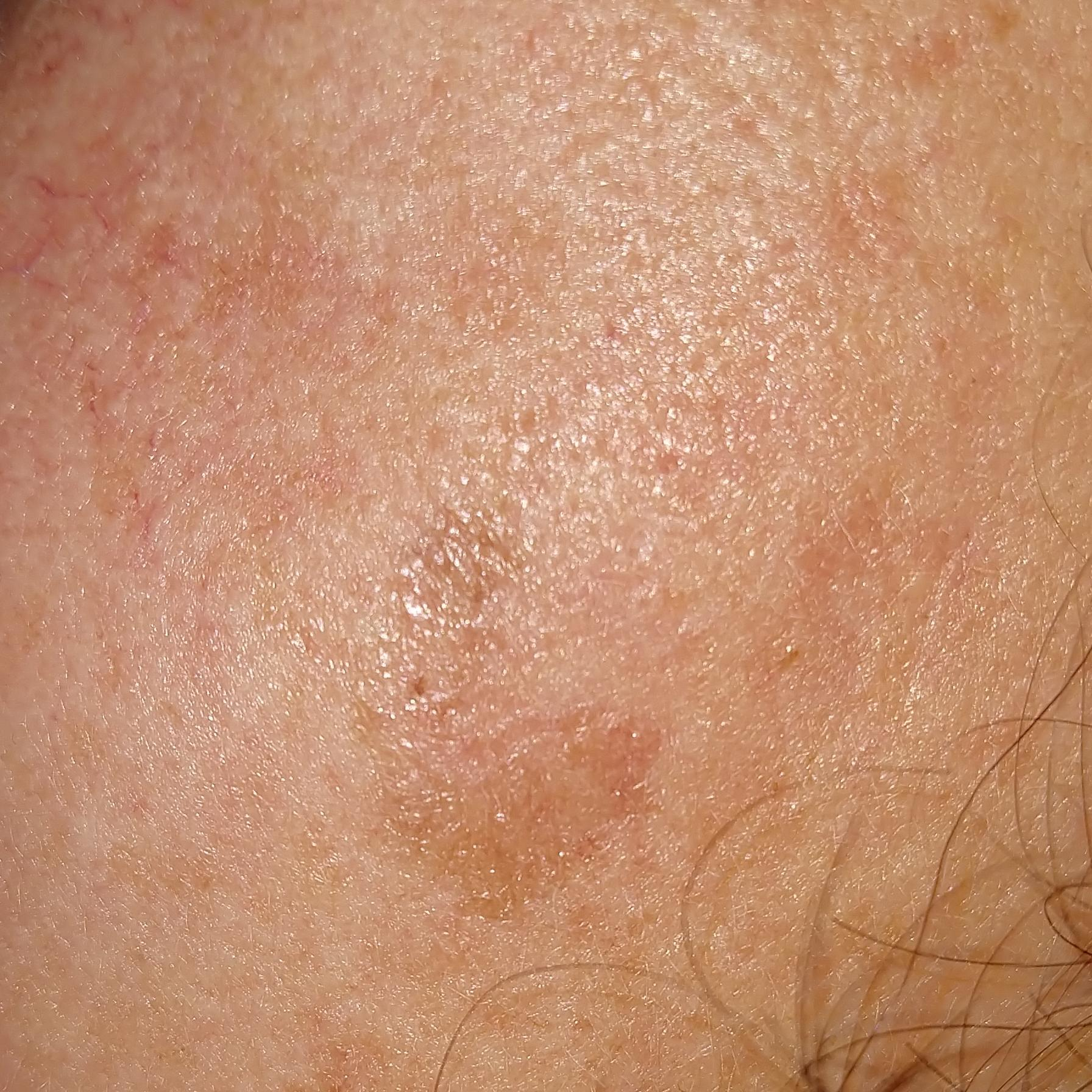{
  "patient": {
    "age": 40
  },
  "image": "smartphone clinical photo",
  "lesion_location": "the face",
  "symptoms": {
    "present": [
      "itching",
      "growth",
      "change in appearance"
    ],
    "absent": [
      "elevation",
      "bleeding"
    ]
  },
  "diagnosis": {
    "name": "actinic keratosis",
    "code": "ACK",
    "malignancy": "indeterminate",
    "confirmation": "clinical consensus"
  }
}